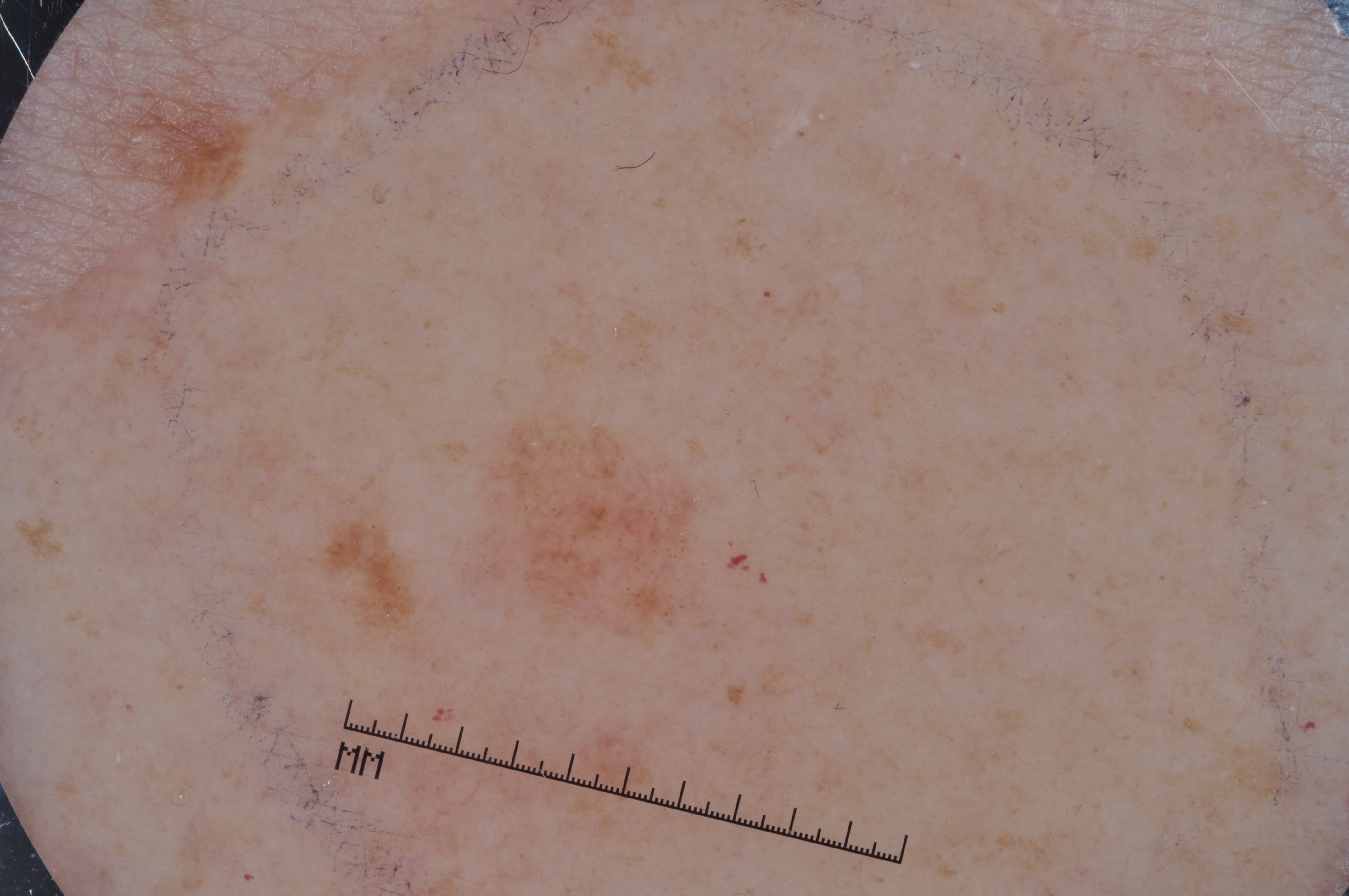Case summary:
- subject — female, aged 28-32
- imaging — dermoscopy of a skin lesion
- dermoscopic pattern — milia-like cysts; absent: pigment network, streaks, and negative network
- lesion bbox — x1=486 y1=394 x2=732 y2=664
- size — small
- diagnostic label — a melanocytic nevus